Symptoms reported: enlargement, itching, bothersome appearance and burning. The patient reports the condition has been present for one to four weeks. The patient is male. The patient described the issue as a rash. The photo was captured at an angle. Texture is reported as rough or flaky, fluid-filled and raised or bumpy. The back of the torso, arm and back of the hand are involved.
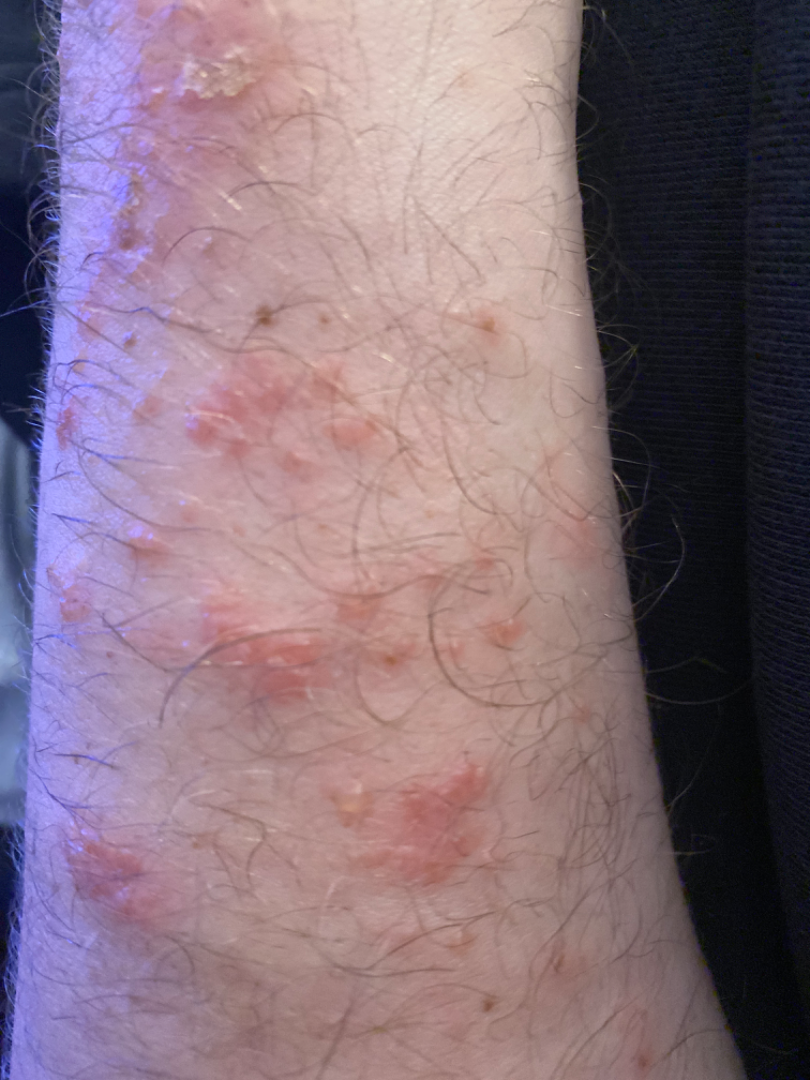Findings:
Allergic Contact Dermatitis (leading); Impetigo (considered); Eczema (considered).